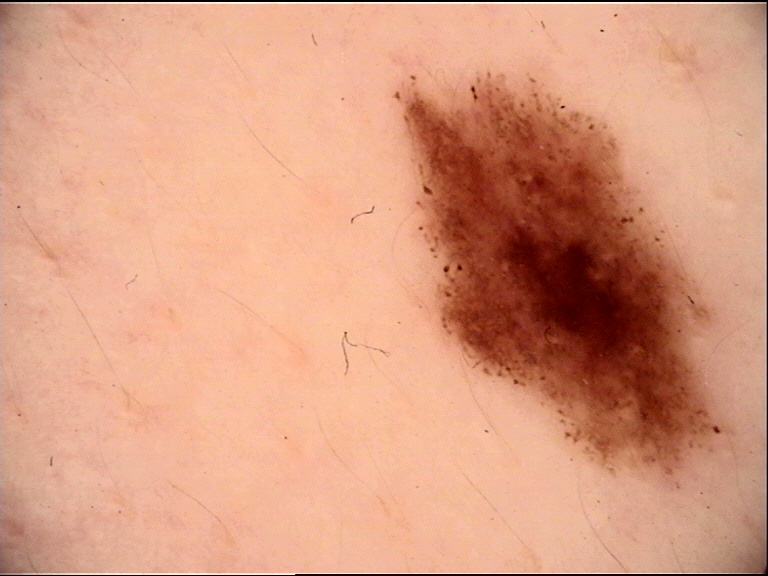diagnostic label: dysplastic junctional nevus (expert consensus).